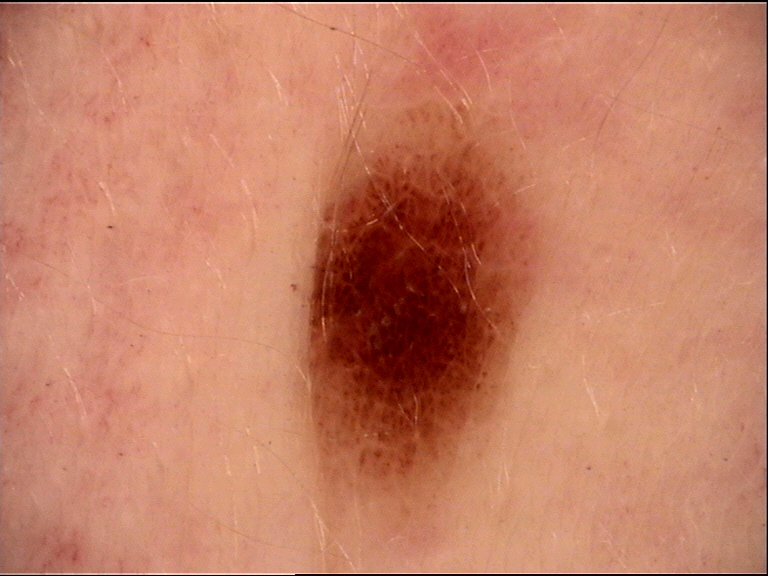assessment = dysplastic junctional nevus (expert consensus).